A dermoscopy image of a single skin lesion.
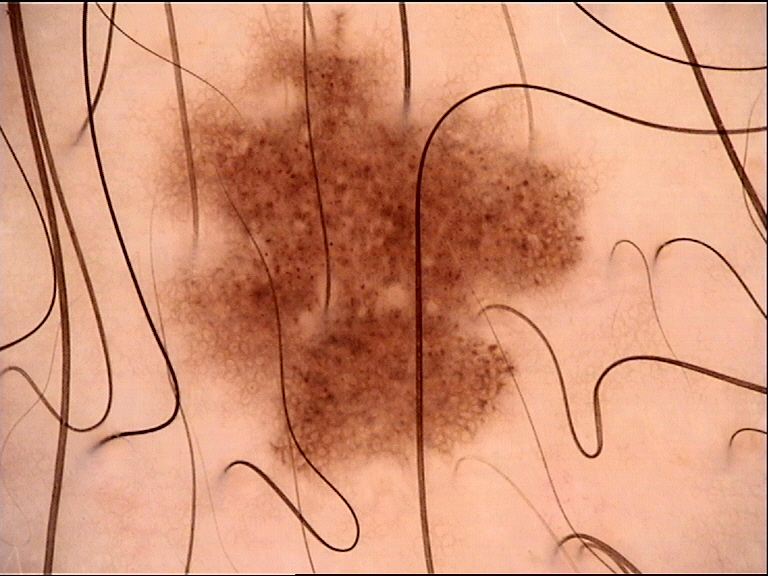Conclusion: Diagnosed as a benign lesion — a dysplastic junctional nevus.